A skin lesion imaged with a dermatoscope.
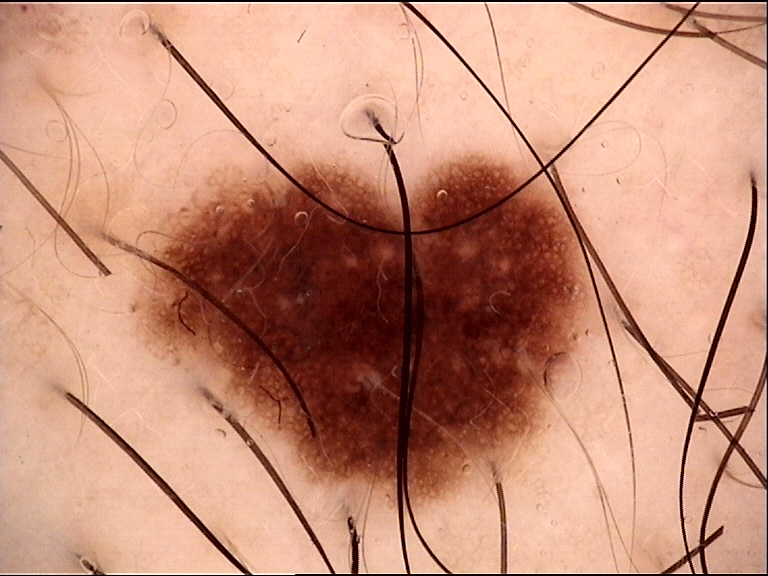Impression: The diagnostic label was a benign lesion — a dysplastic junctional nevus.